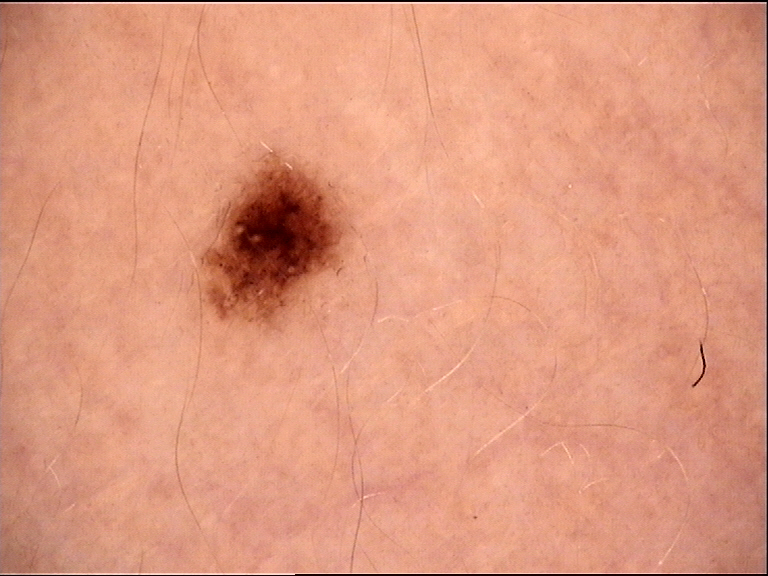| feature | finding |
|---|---|
| class | junctional nevus (expert consensus) |